The affected area is the back of the hand · the patient reported no systemic symptoms · the subject is a male aged 50–59 · reported lesion symptoms include itching · present for less than one week · self-categorized by the patient as a rash · Fitzpatrick I · texture is reported as raised or bumpy · an image taken at an angle: 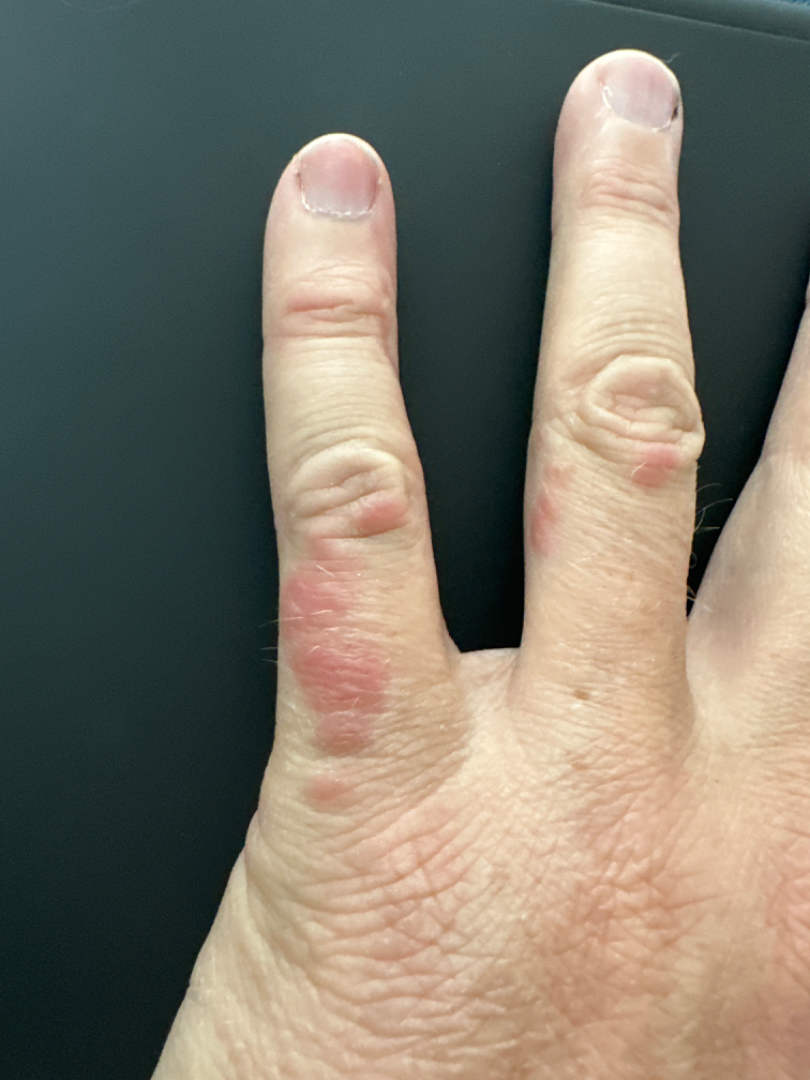assessment — three independent reviewers: the impression was split between Eczema and Allergic Contact Dermatitis; less likely is Scabies.